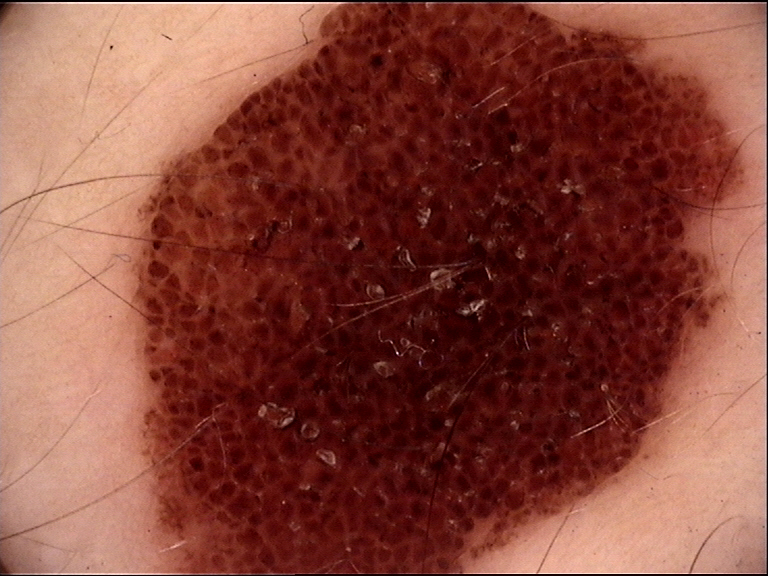The diagnosis was a compound nevus.